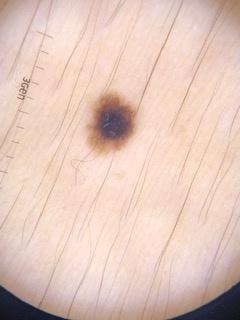Conclusion: Confirmed on histopathology as a nevus.